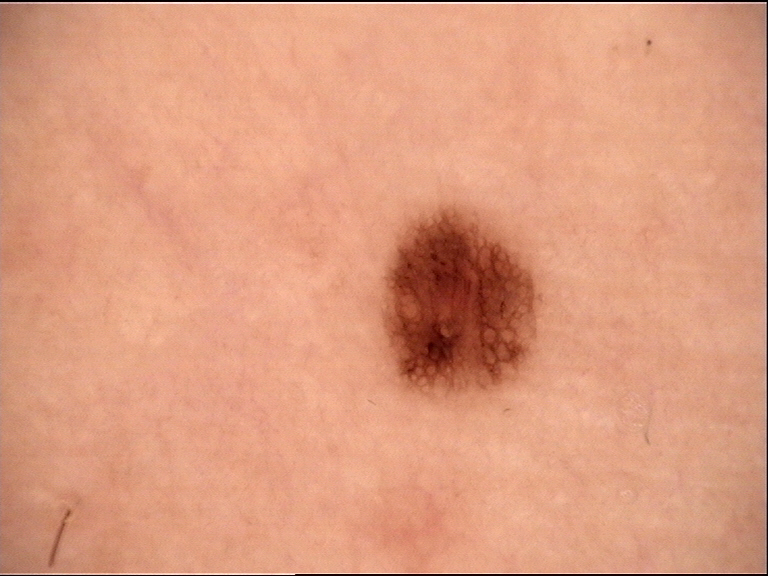image: dermatoscopy; class: dysplastic junctional nevus (expert consensus).